A female subject in their mid-40s · a skin lesion imaged with a dermatoscope.
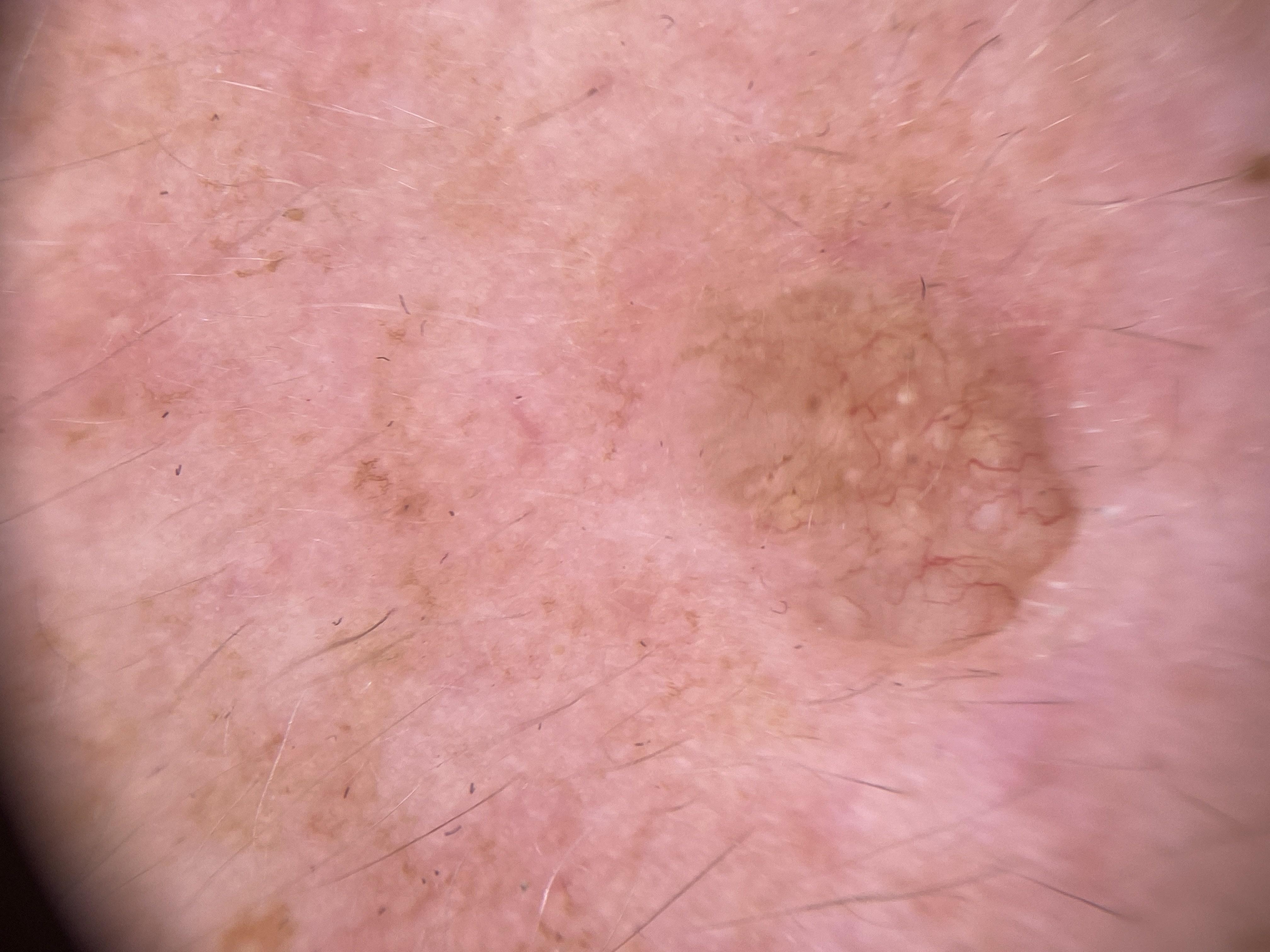Notes:
- site — the head or neck
- diagnostic label — Basal cell carcinoma (biopsy-proven)